Located on the front of the torso, arm and head or neck · this is a close-up image · the subject is a male aged 18–29 — 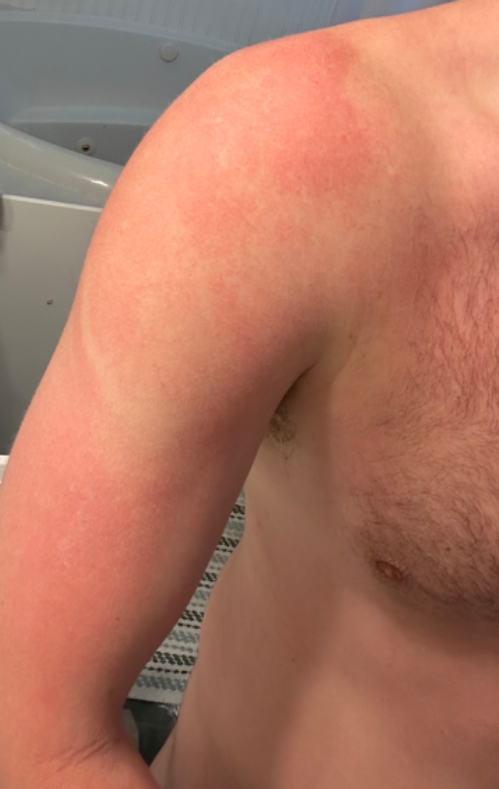Q: What was the assessment?
A: indeterminate
Q: Patient's own categorization?
A: a rash
Q: Texture?
A: flat